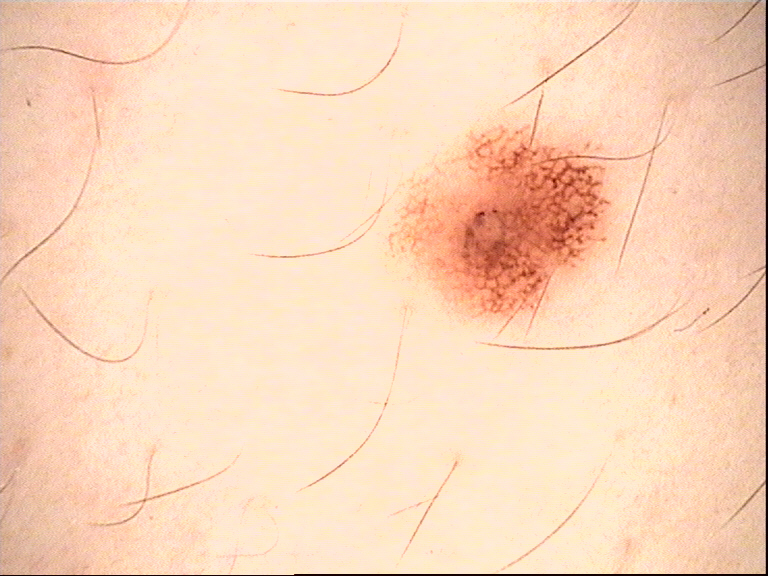Conclusion:
The diagnosis was a benign lesion — a dysplastic junctional nevus.